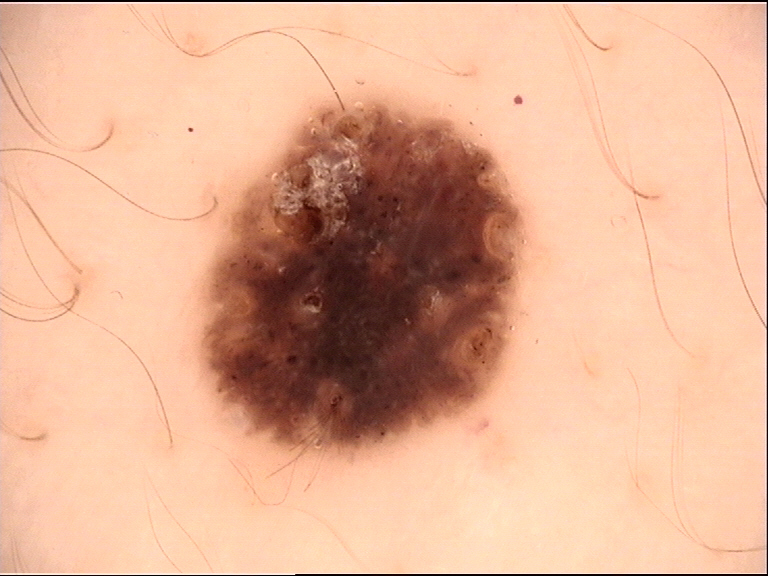Dermoscopy of a skin lesion. Labeled as a benign lesion — a dysplastic compound nevus.